The lesion involves the leg and arm · male subject, age 18–29 · close-up view:
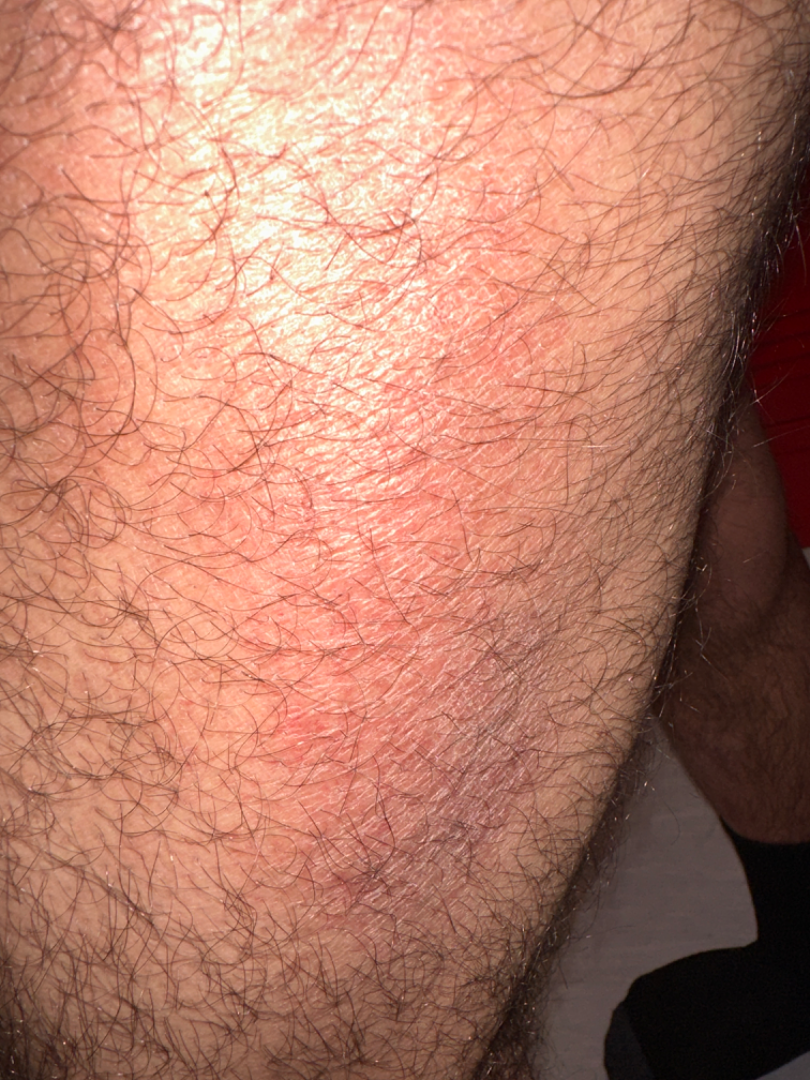Symptoms reported: bleeding, itching, darkening and enlargement. The patient notes the condition has been present for one to three months. The patient described the issue as a rash. The lesion is described as rough or flaky and raised or bumpy. Skin tone: Fitzpatrick phototype II. No constitutional symptoms were reported. Favoring Eczema; possibly Irritant Contact Dermatitis.